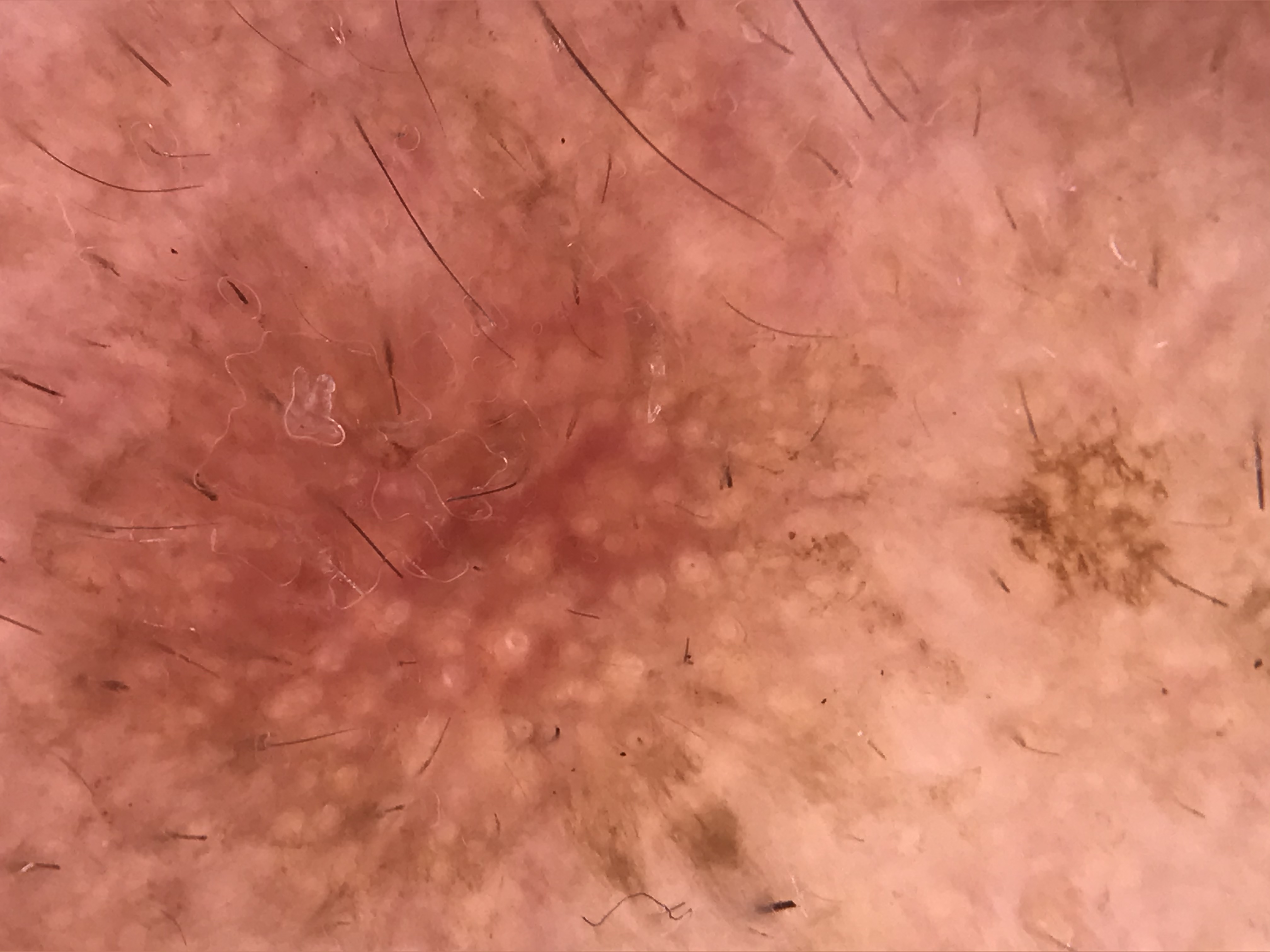Diagnosed as an actinic keratosis.